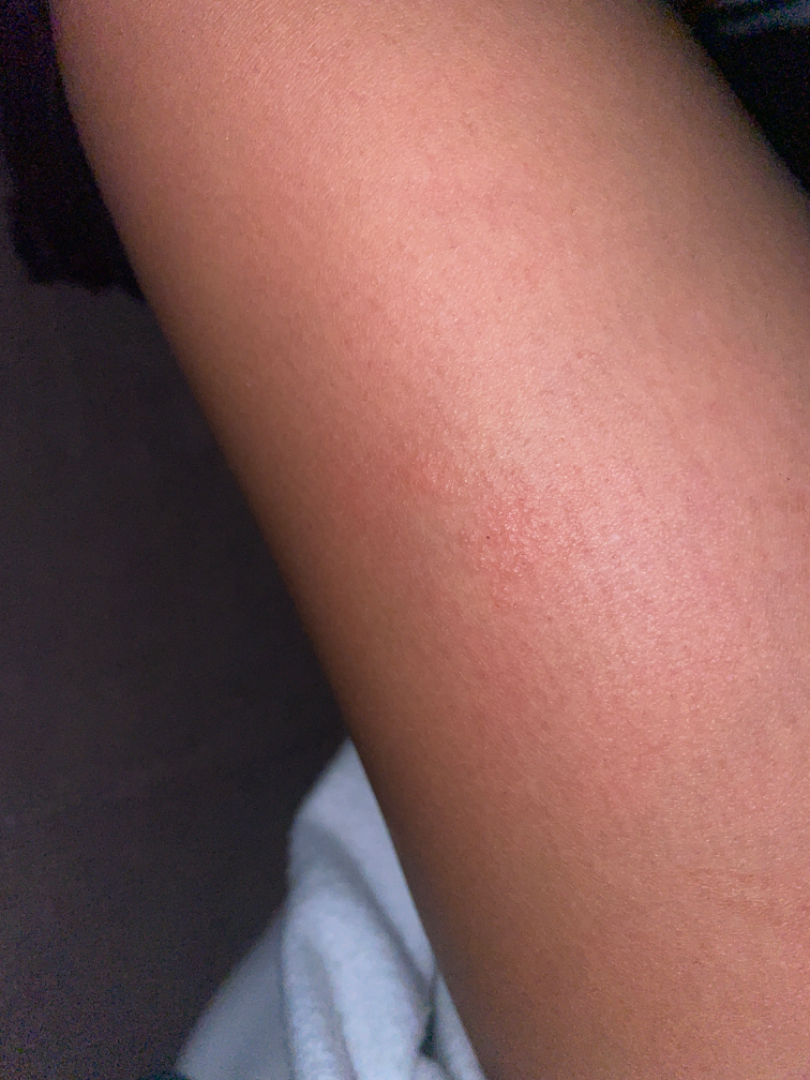{"shot_type": "at an angle", "body_site": "leg", "duration": "about one day", "systemic_symptoms": "mouth sores", "skin_tone": {"monk_skin_tone": [2, 5]}, "patient_category": "a rash", "symptoms": "none reported", "texture": "raised or bumpy", "differential": {"leading": ["Allergic Contact Dermatitis"], "considered": ["Eczema"]}}